A dermoscopic photograph of a skin lesion.
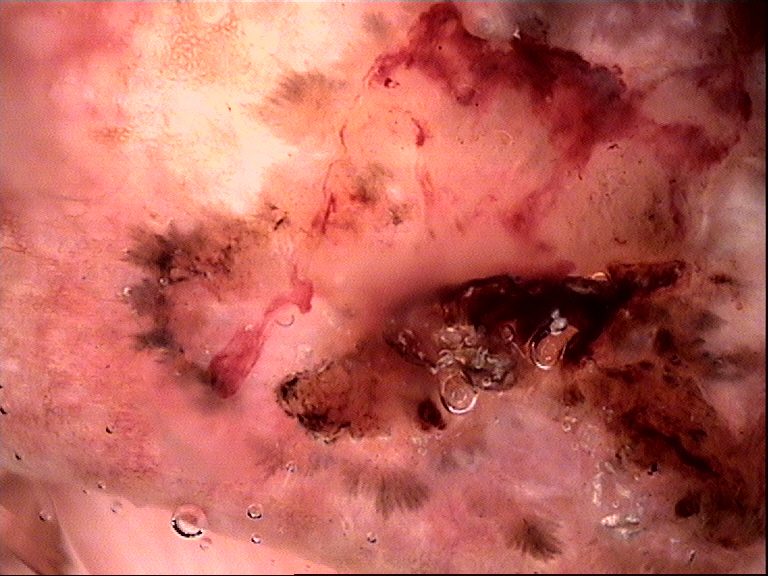lesion type: keratinocytic, label: basal cell carcinoma (biopsy-proven).